No associated systemic symptoms reported. The lesion involves the leg. The contributor reports itching, burning, bothersome appearance and pain. The contributor reports the lesion is raised or bumpy and rough or flaky. The photo was captured at an angle. Skin tone: Fitzpatrick skin type II — 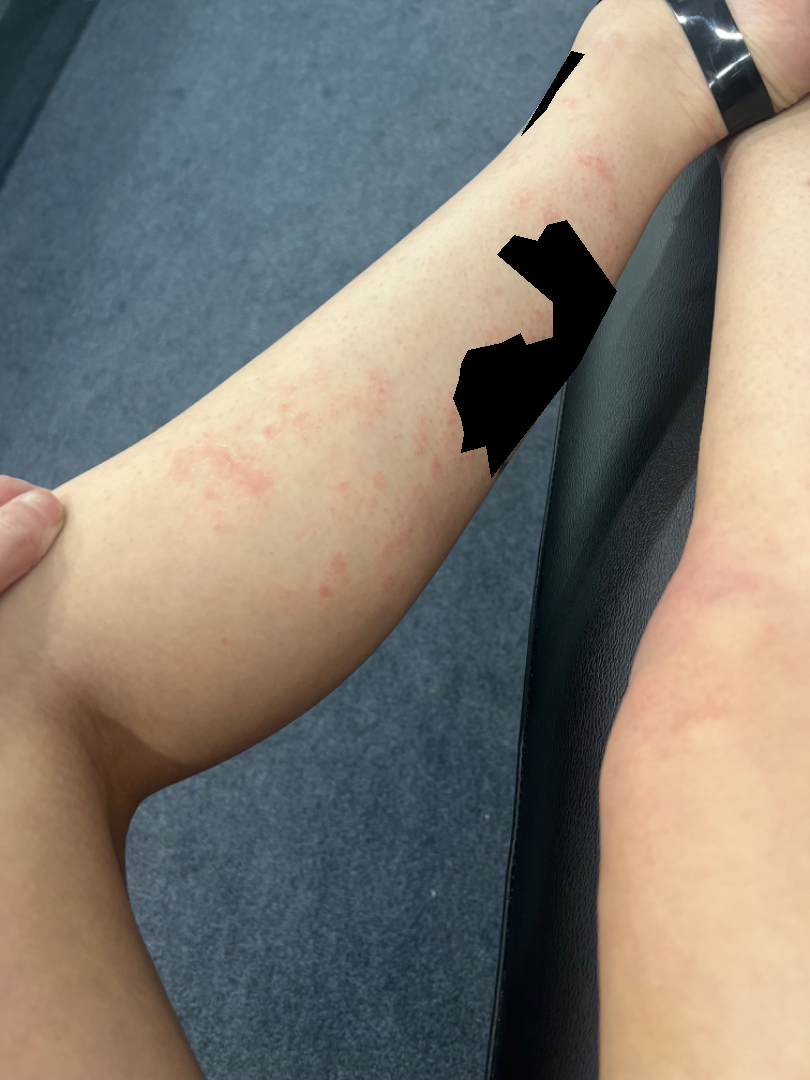Impression: The favored diagnosis is Eczema; also raised was Allergic Contact Dermatitis.